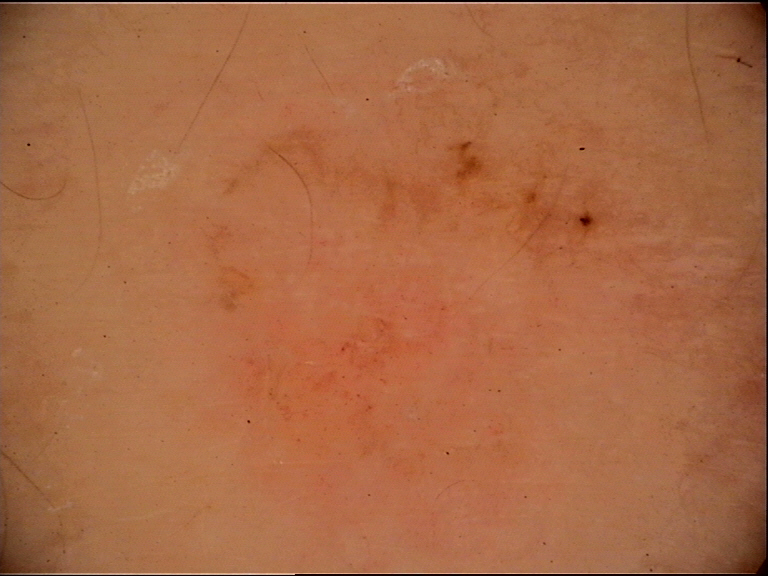Histopathology confirmed a basal cell carcinoma.